The photograph was taken at an angle; the patient notes the lesion is fluid-filled; female contributor, age 40–49; the affected area is the top or side of the foot; symptoms reported: burning and itching; present for about one day:
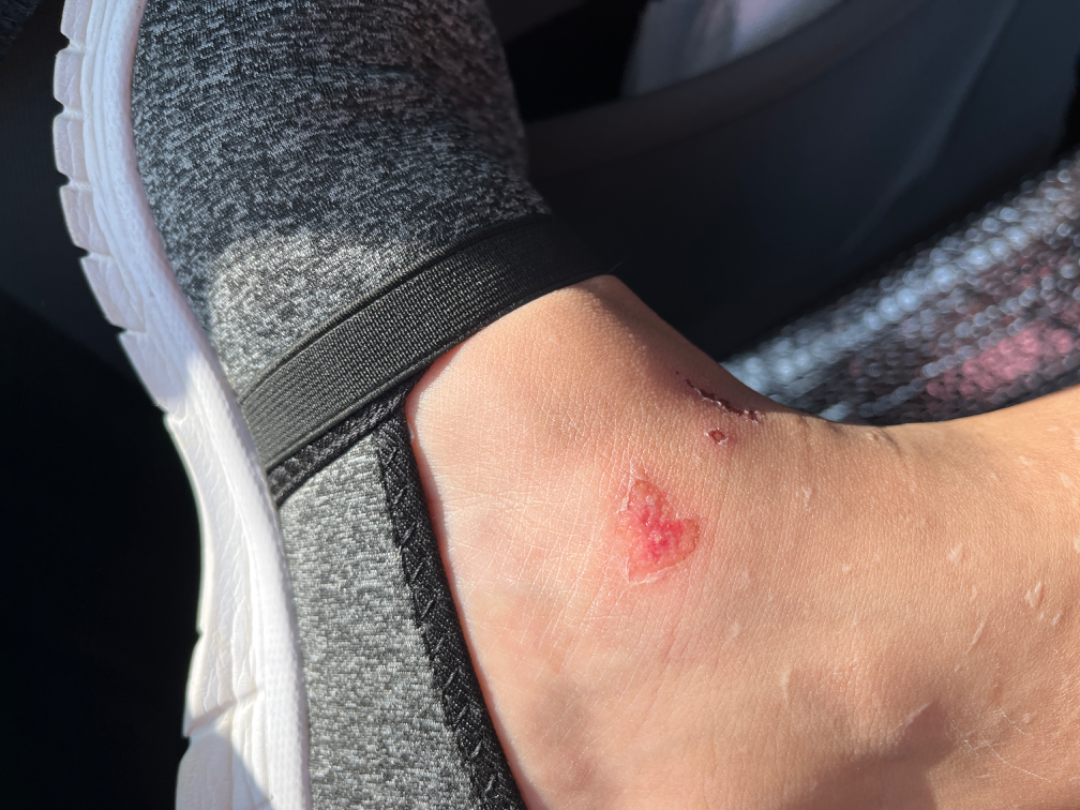Q: What was the assessment?
A: indeterminate from the photograph